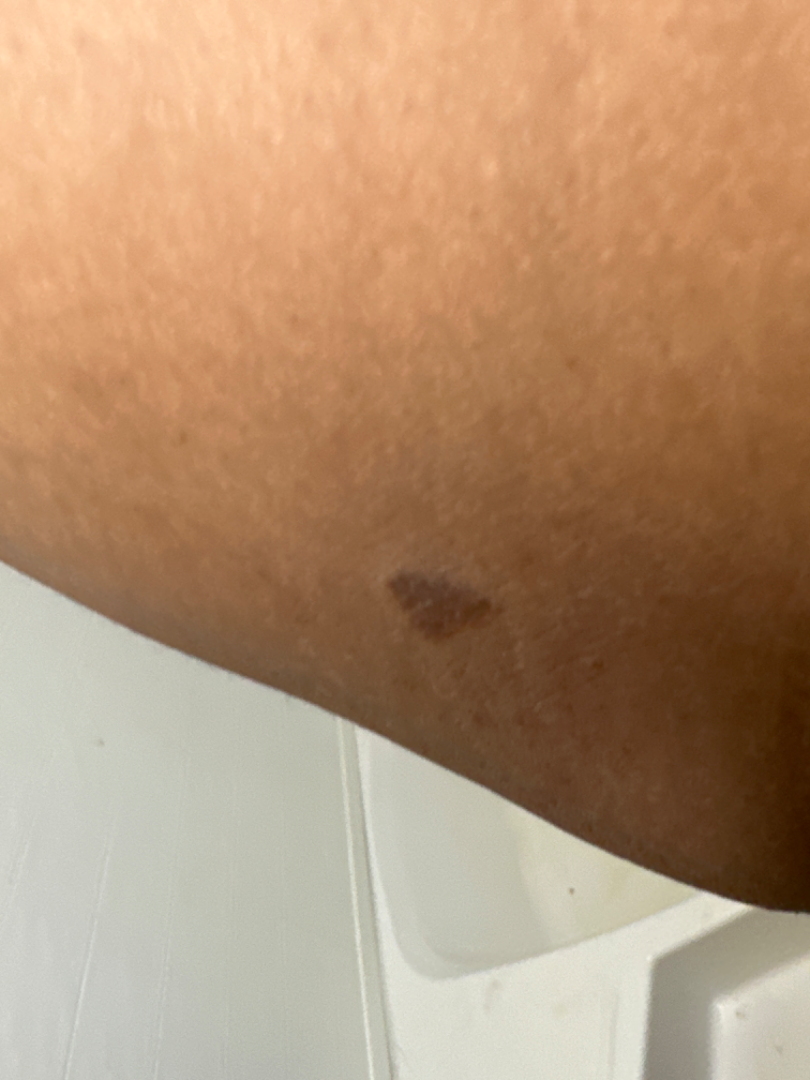Patient information:
The patient described the issue as a rash. The lesion involves the arm. Close-up view. The condition has been present for one to three months. Texture is reported as flat and rough or flaky.
Review:
On remote review of the image, the leading consideration is SK/ISK; possibly Eczema.